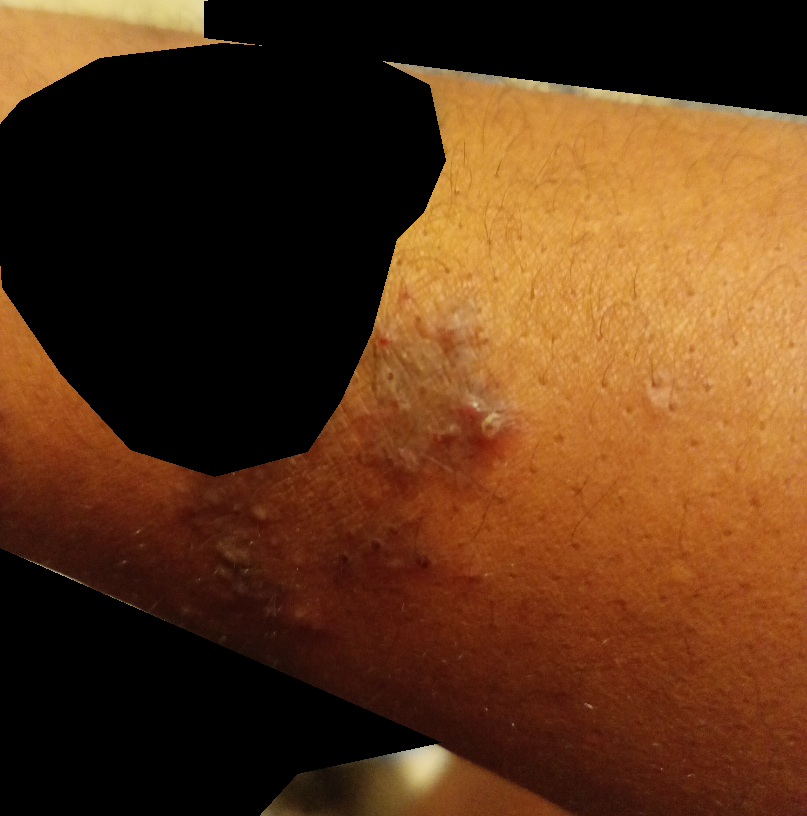shot type: close-up, skin tone: Fitzpatrick V, differential diagnosis: the leading consideration is Majocchi granuloma; possibly Eczema; also raised was Cutaneous sarcoidosis.